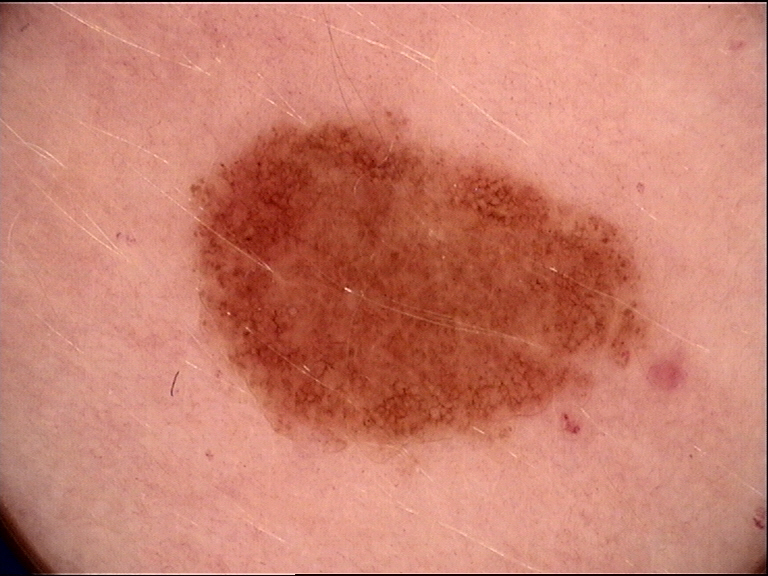Q: What is the imaging modality?
A: dermoscopy
Q: What was the diagnostic impression?
A: dysplastic junctional nevus (expert consensus)